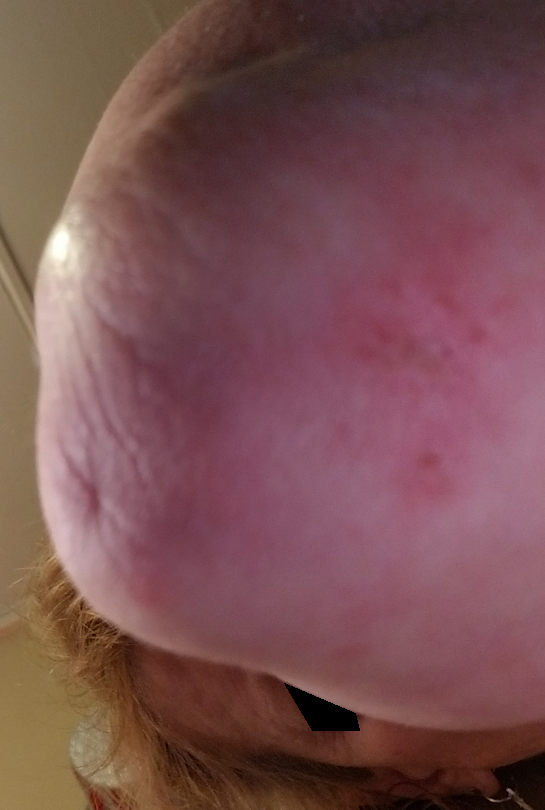The reviewer was unable to grade this case for skin condition.
Located on the arm.
The subject is a female aged 60–69.
Close-up view.